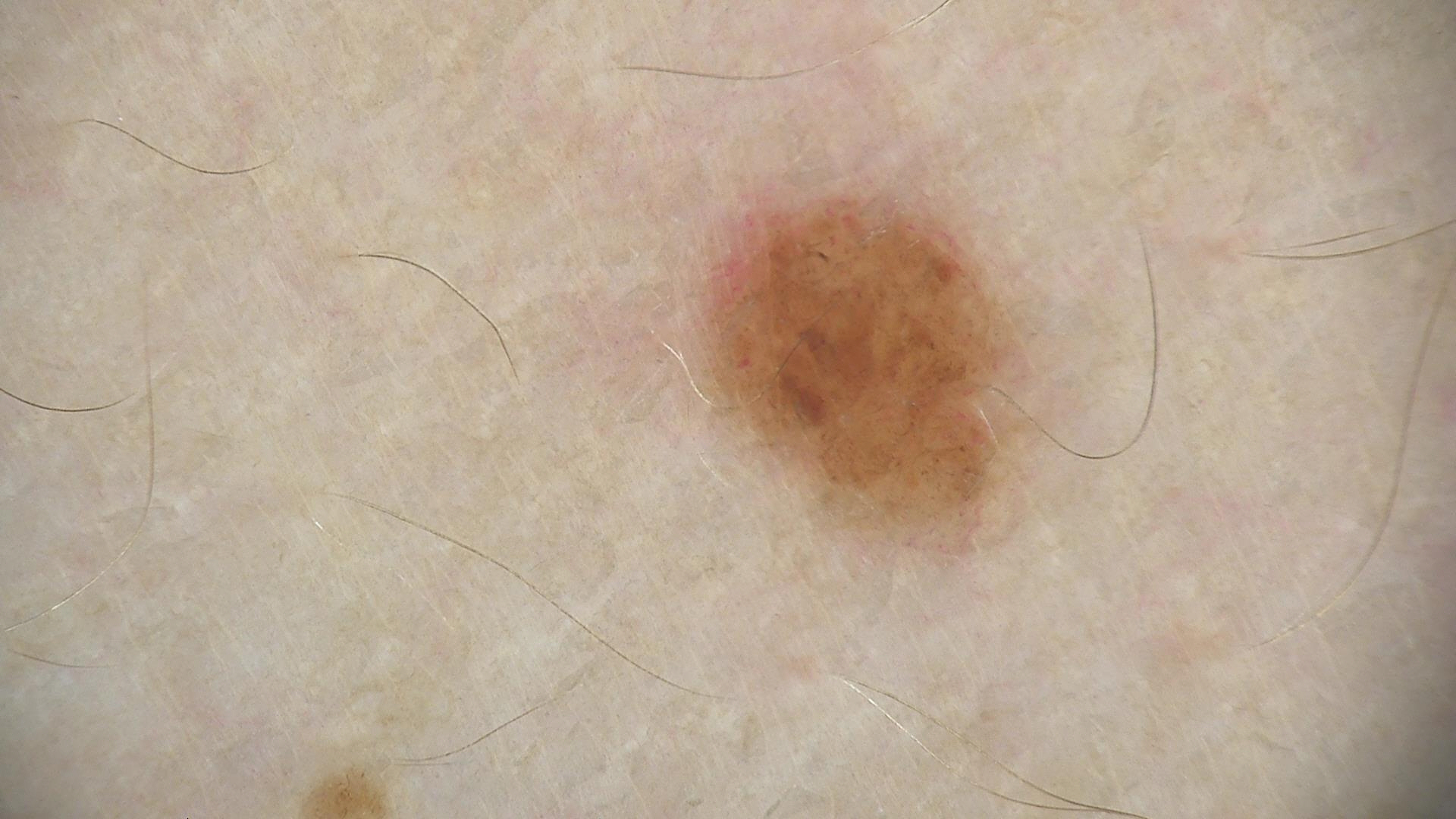A dermoscopic photograph of a skin lesion. The diagnosis was a benign lesion — a dysplastic compound nevus.